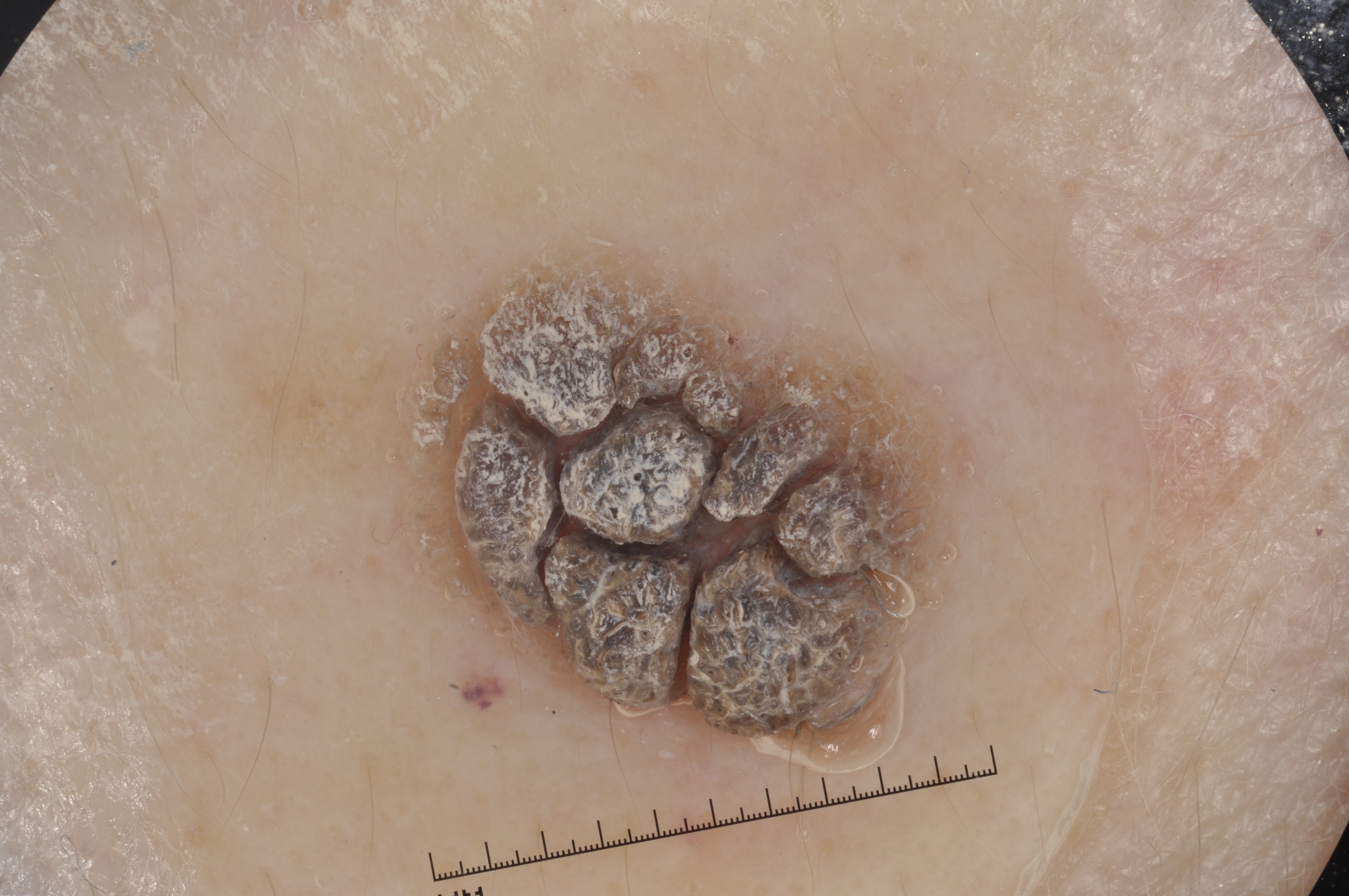Q: Patient demographics?
A: female, in their 60s
Q: What kind of image is this?
A: dermoscopic image
Q: Which assessed dermoscopic features were absent?
A: streaks, negative network, pigment network, and milia-like cysts
Q: Lesion extent?
A: moderate
Q: What is the lesion's bounding box?
A: 411 273 970 735
Q: What is the diagnosis?
A: a seborrheic keratosis, a benign lesion